The patient is a female aged 30–39; located on the head or neck, leg, palm and arm; this image was taken at an angle — 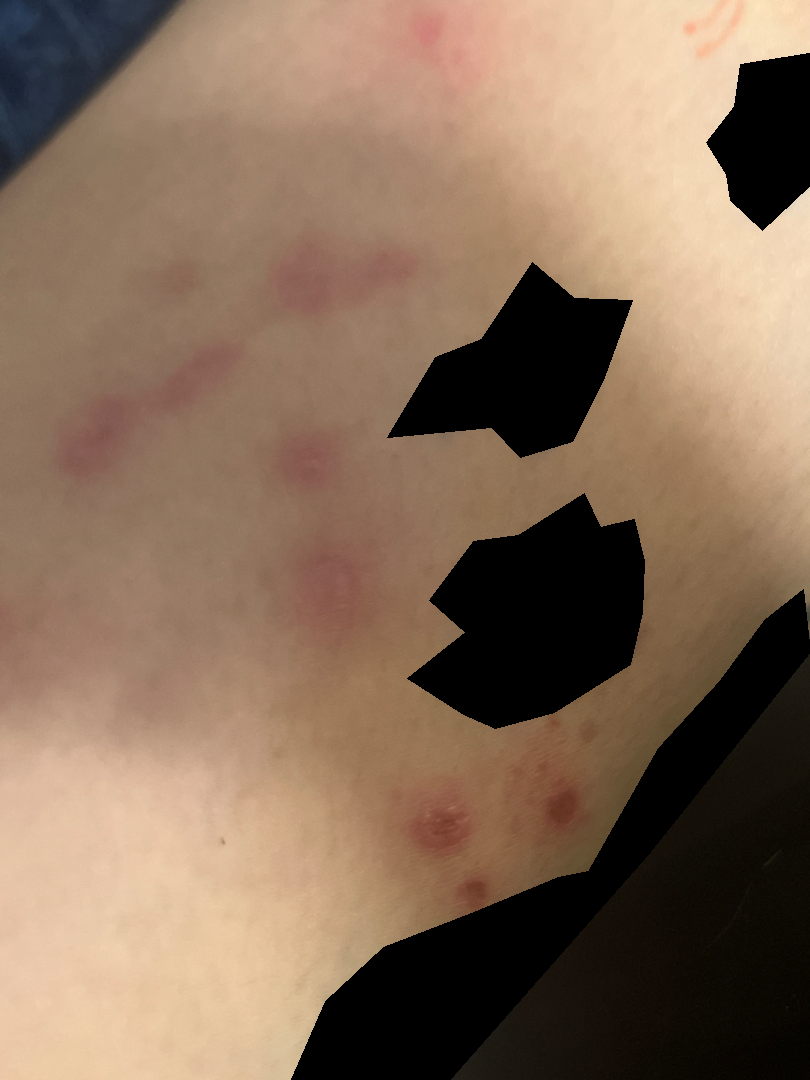Background: The patient described the issue as a rash. The lesion is described as fluid-filled and raised or bumpy. The condition has been present for since childhood. Findings: The reviewing dermatologist's impression was: Prurigo nodularis (0.67); Folliculitis (0.33).